The lesion involves the leg and arm; the photograph was taken at an angle; the lesion is described as raised or bumpy; the patient notes the condition has been present for about one day.
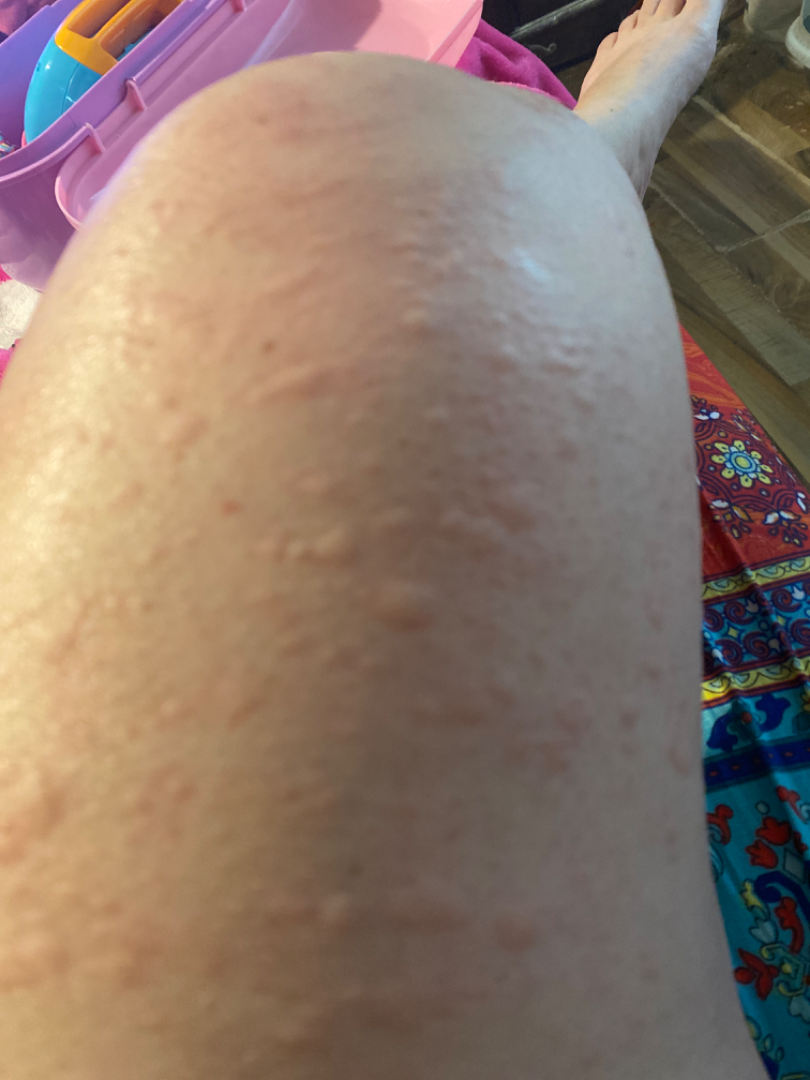The favored diagnosis is Urticaria; an alternative is Eczema; a remote consideration is Leukocytoclastic Vasculitis.